Fitzpatrick II; a patient approximately 55 years of age; a skin lesion imaged with contact-polarized dermoscopy:
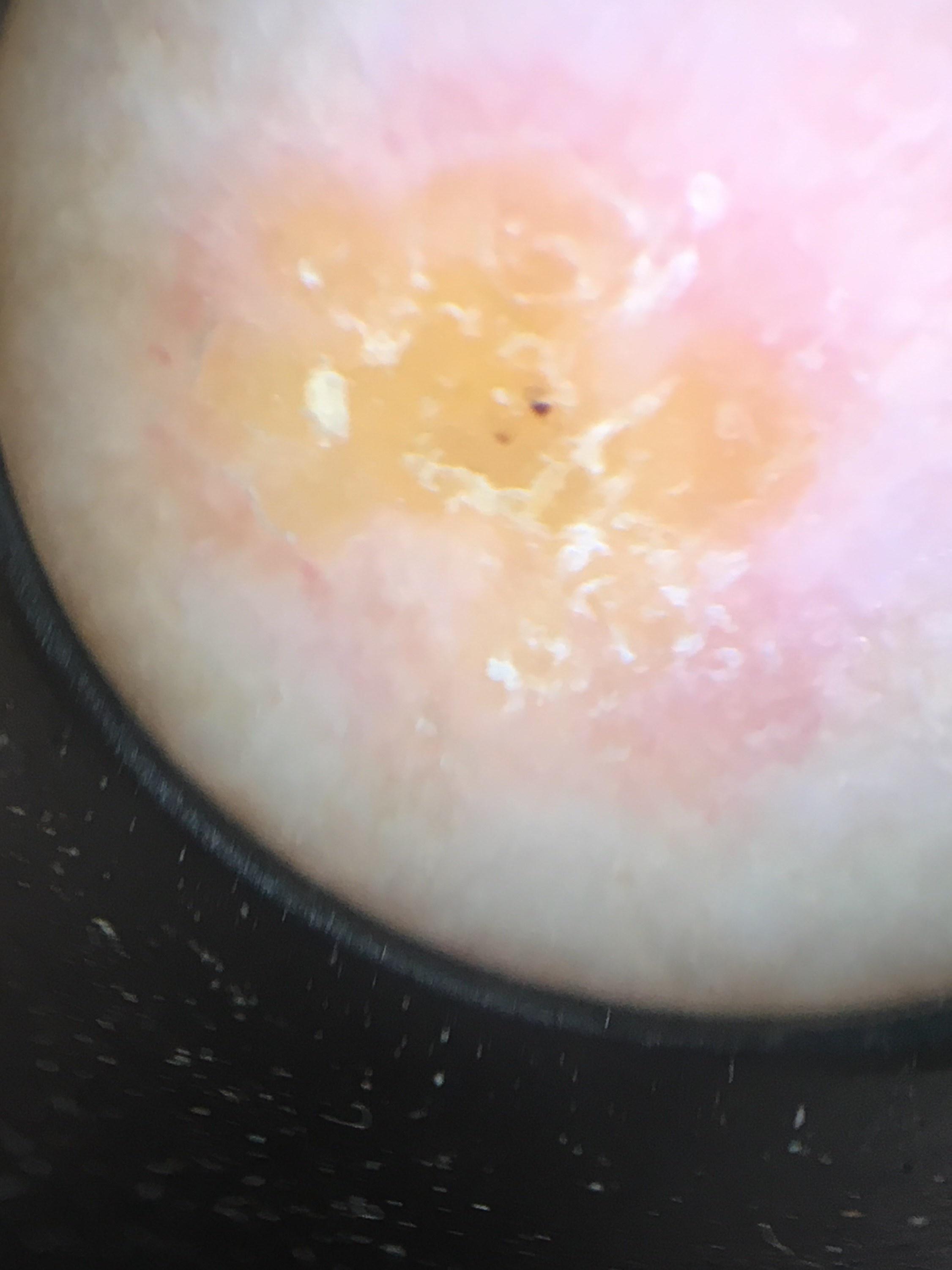Conclusion:
On biopsy, the diagnosis was a tumor of follicular differentiation — a basal cell carcinoma.